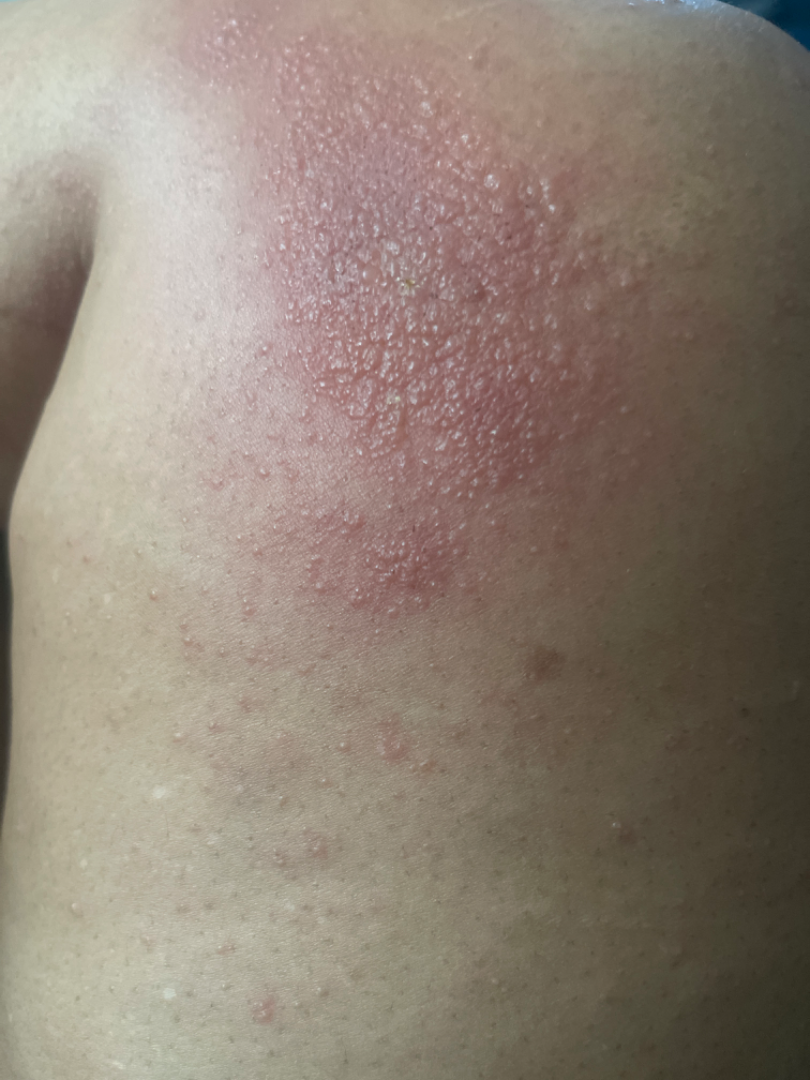The skin condition could not be confidently assessed from this image. The lesion involves the leg and head or neck. No associated systemic symptoms reported. The patient considered this a rash. Reported lesion symptoms include bothersome appearance, enlargement and itching. The patient indicates the lesion is raised or bumpy. The photograph is a close-up of the affected area. FST IV. The patient indicates the condition has been present for less than one week.